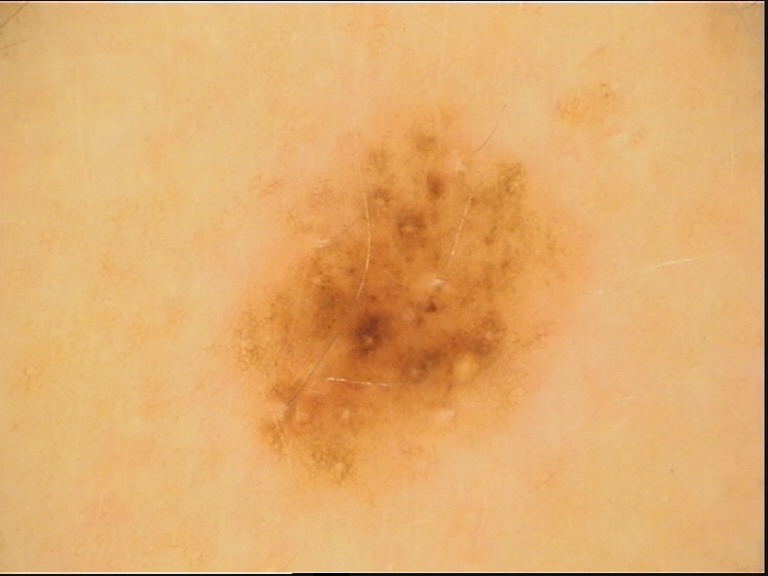imaging=dermoscopy
label=dysplastic junctional nevus (expert consensus)